A dermatoscopic image of a skin lesion.
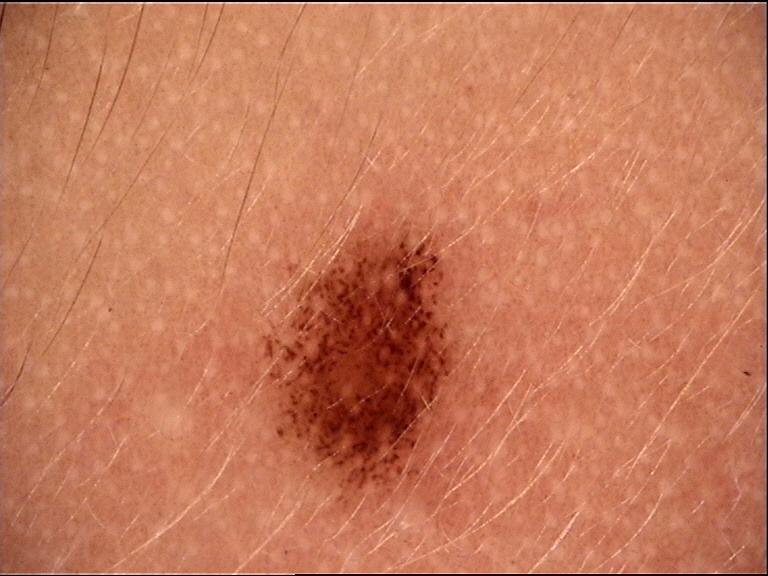* class · dysplastic junctional nevus (expert consensus)